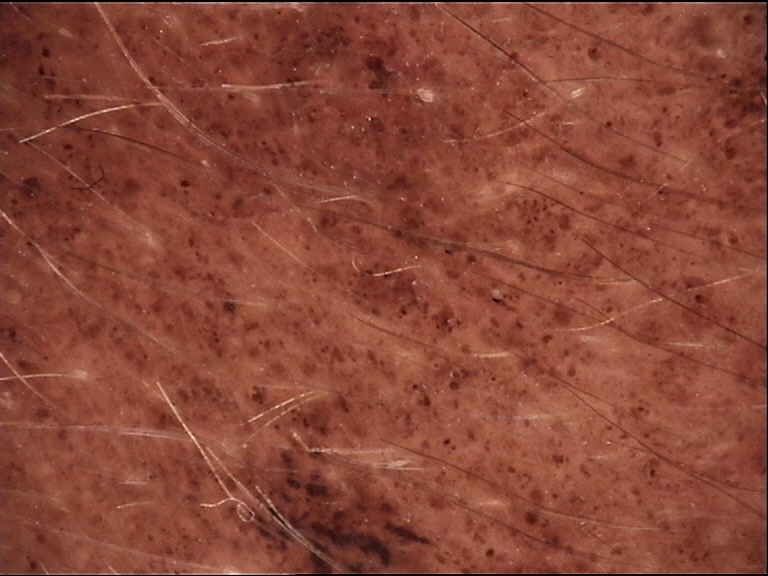* classification — banal
* label — congenital compound nevus (expert consensus)